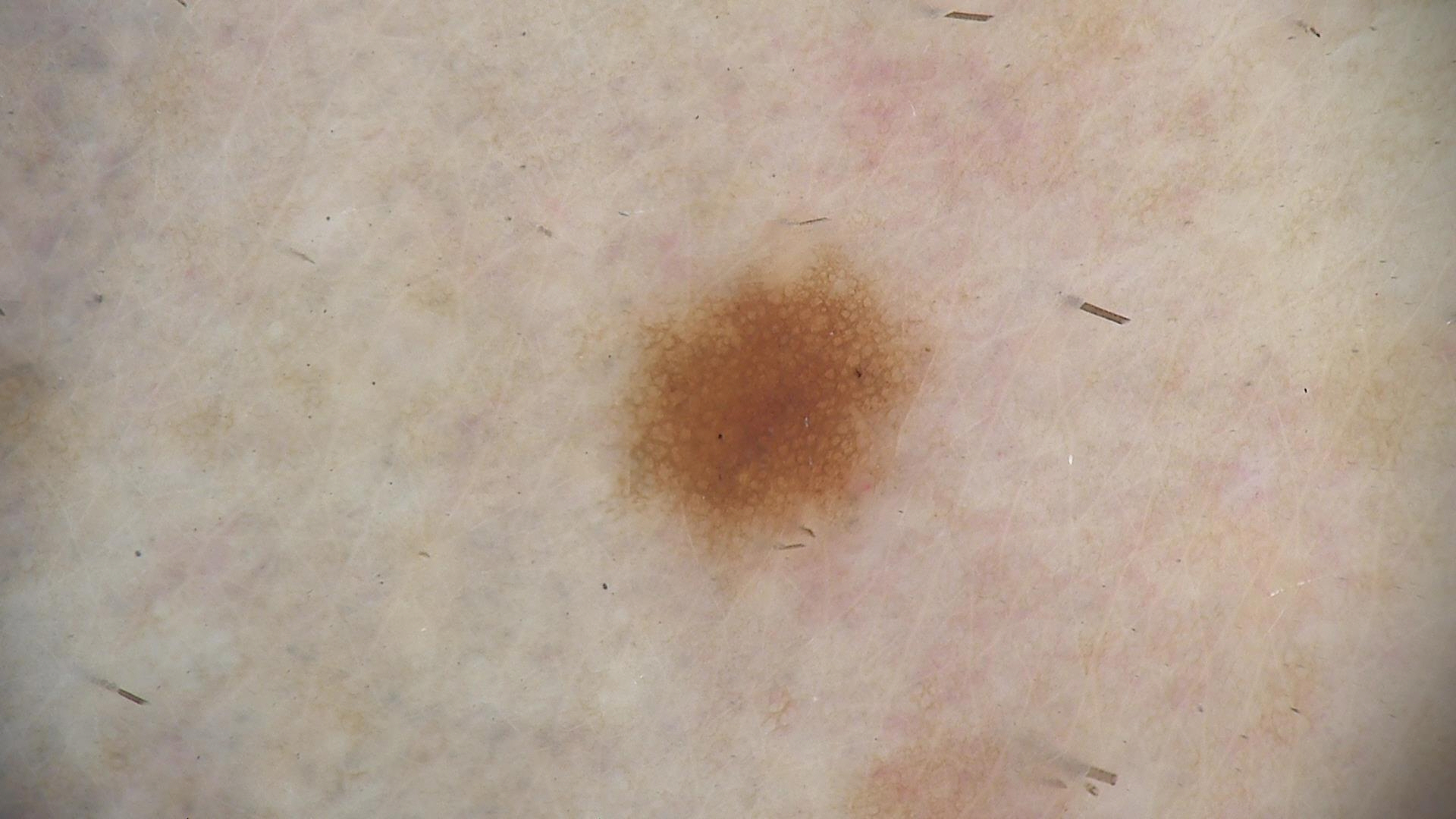* modality · dermatoscopy
* class · dysplastic junctional nevus (expert consensus)